A male patient roughly 40 years of age:
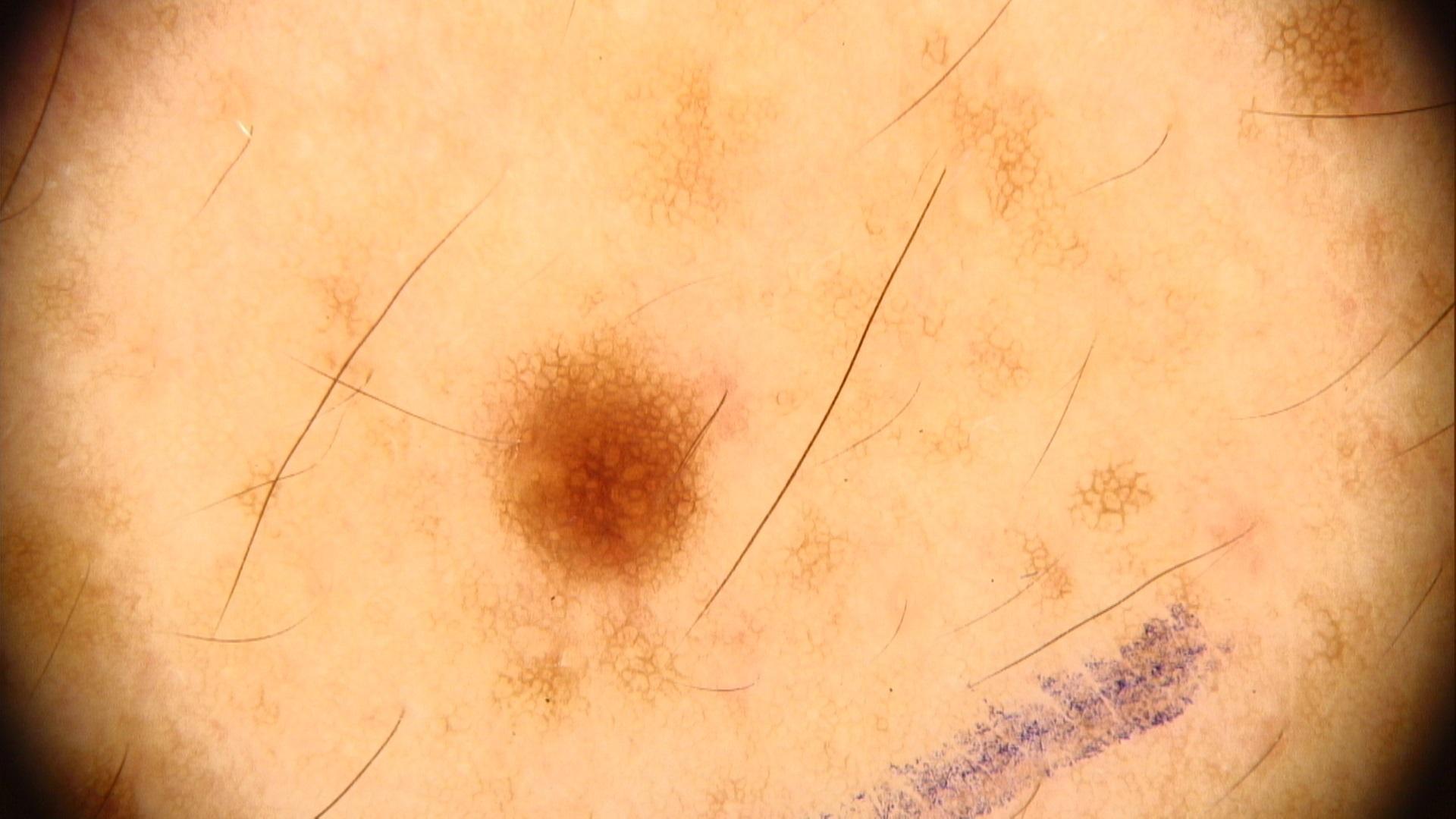assessment: Nevus